A dermatoscopic image of a skin lesion — 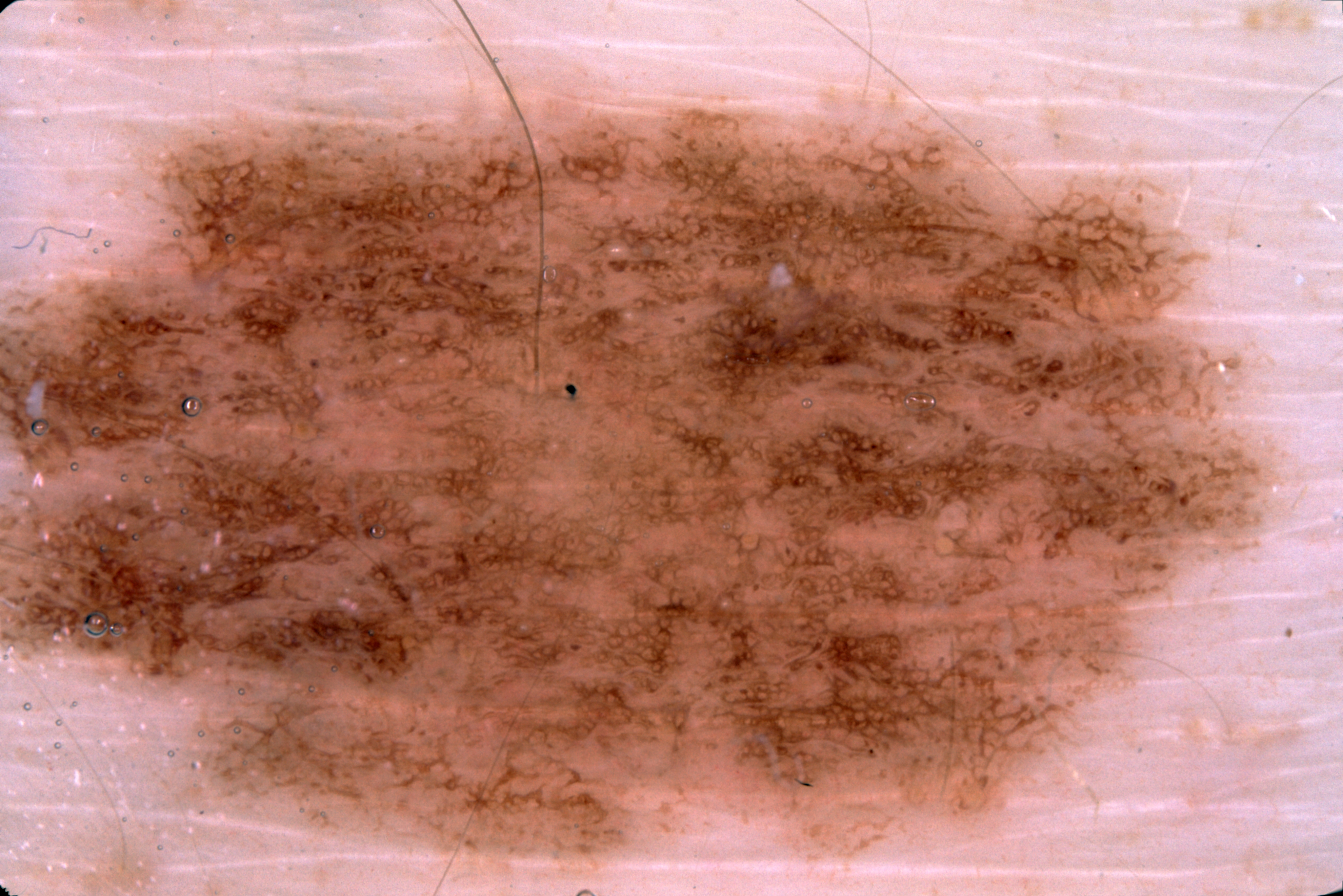dermoscopic pattern — milia-like cysts and pigment network; absent: negative network and streaks | size — large | bounding box — left=0, top=91, right=1280, bottom=875 | lesion margin — clipped at the frame edge | assessment — a melanocytic nevus.